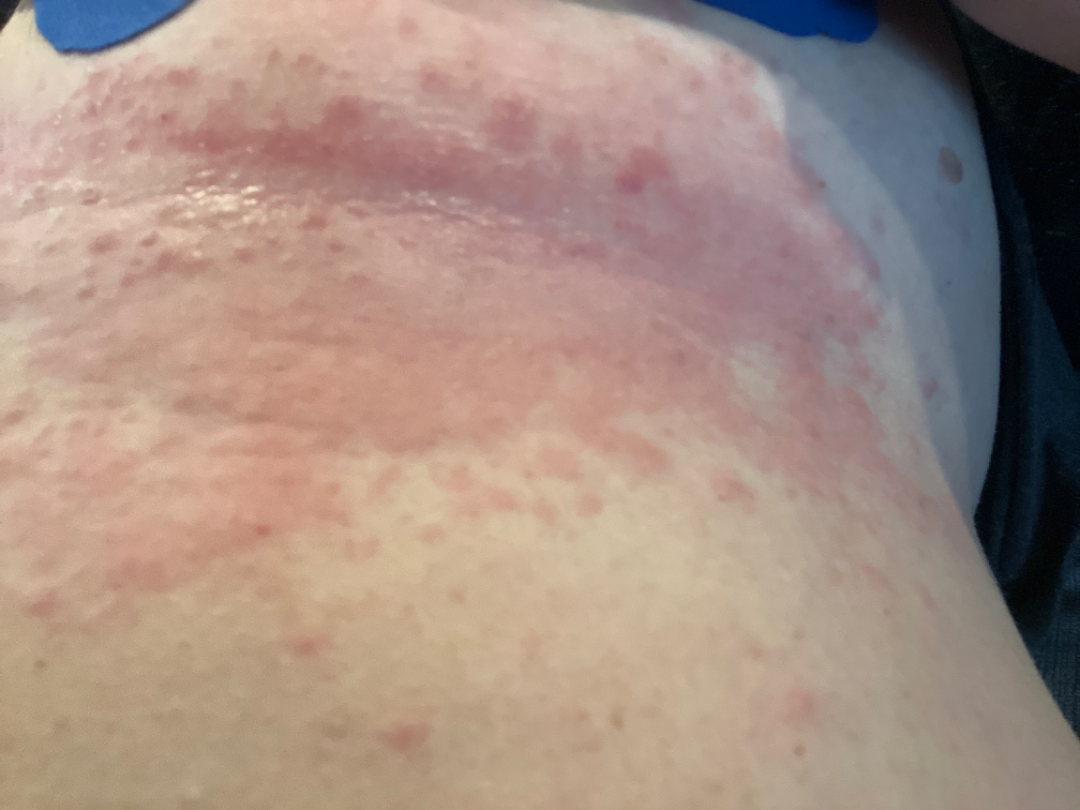The affected area is the front of the torso.
This is a close-up image.
On remote dermatologist review, the leading consideration is Candida intertrigo; the differential also includes Allergic Contact Dermatitis; less probable is Psoriasis.